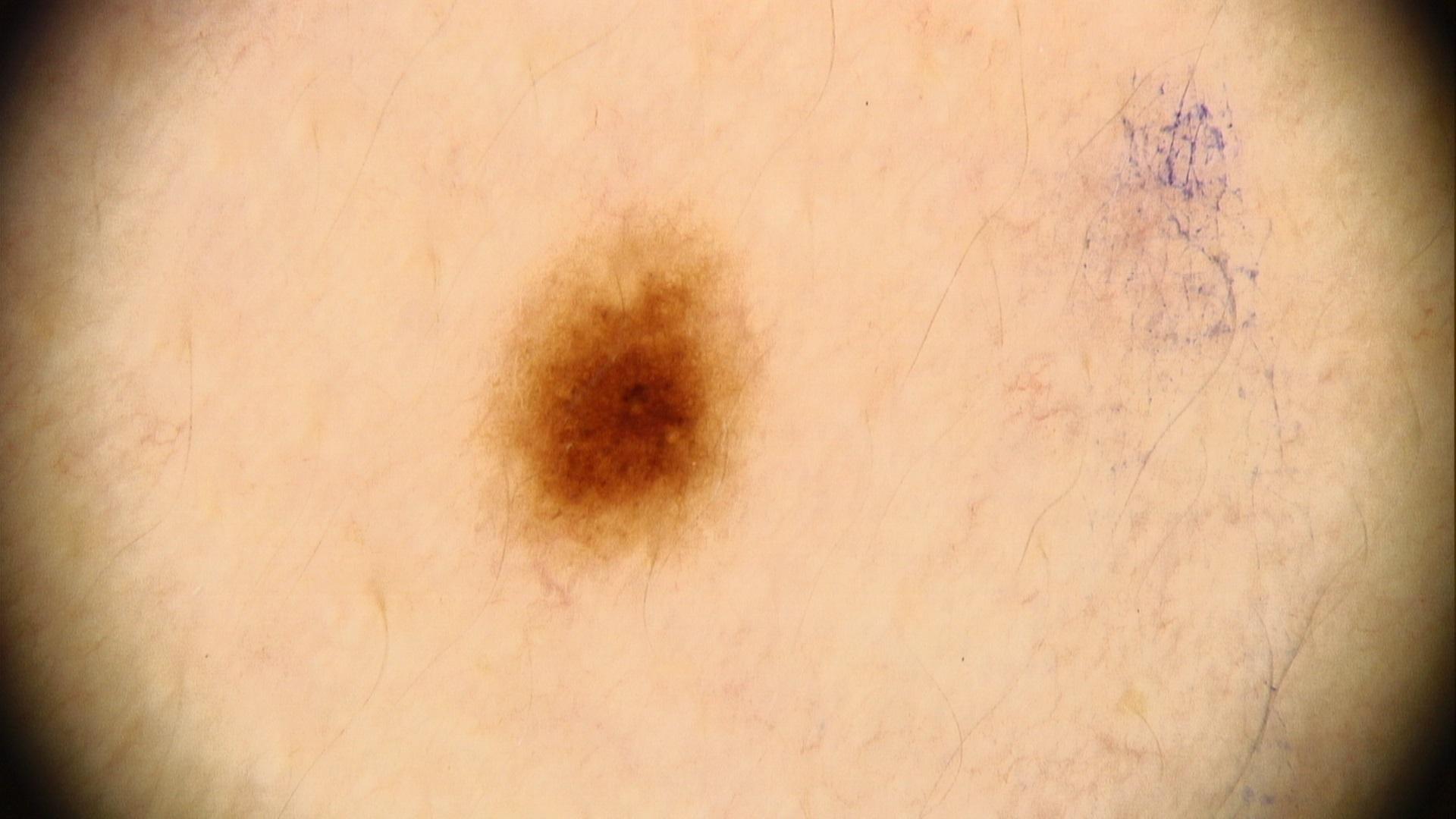The chart records melanoma in a first-degree relative. Recorded as Fitzpatrick phototype III. A skin lesion imaged with a dermatoscope. A female patient approximately 20 years of age. Clinically diagnosed as a melanocytic lesion — a nevus.